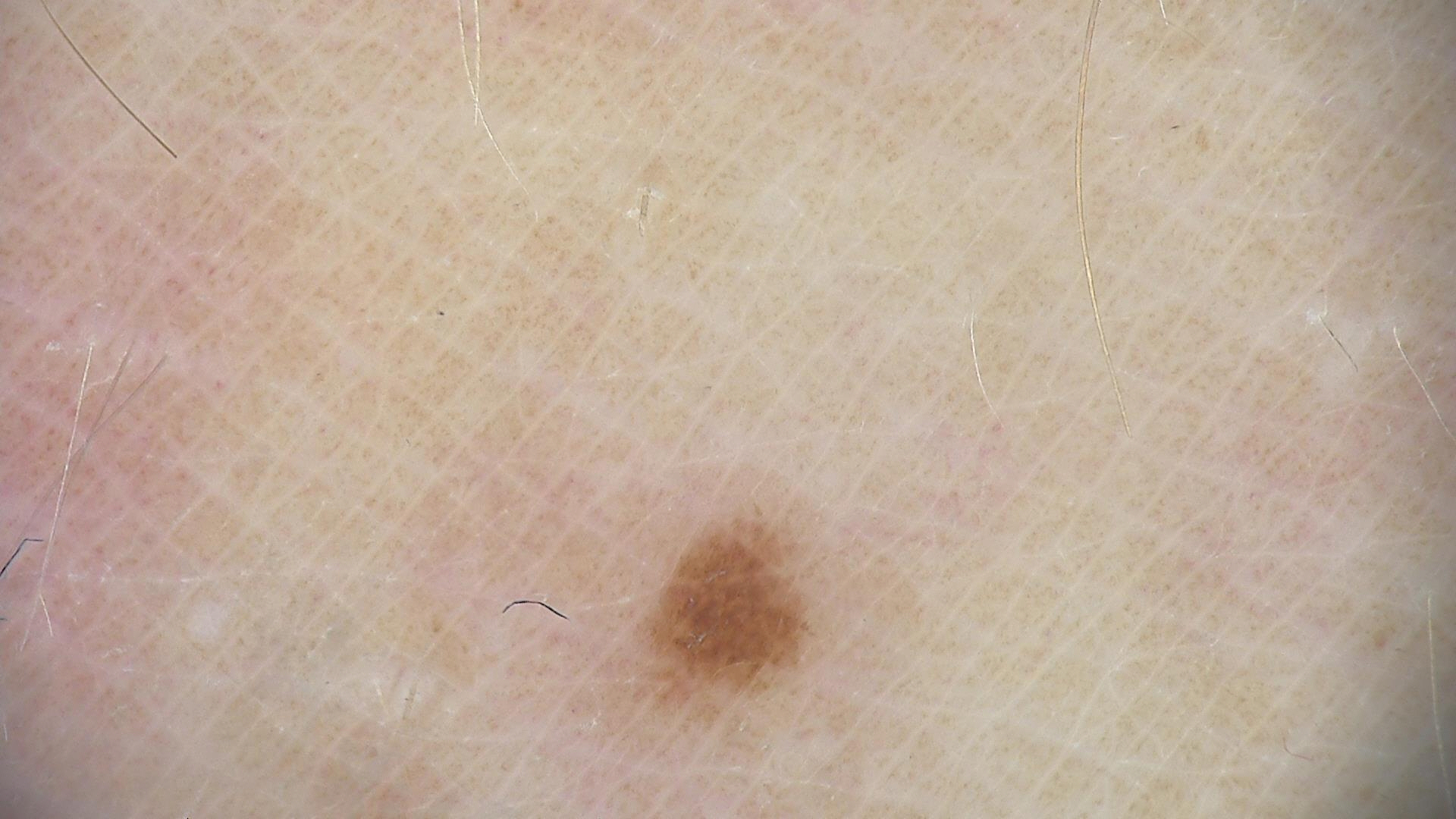class = compound nevus (expert consensus).